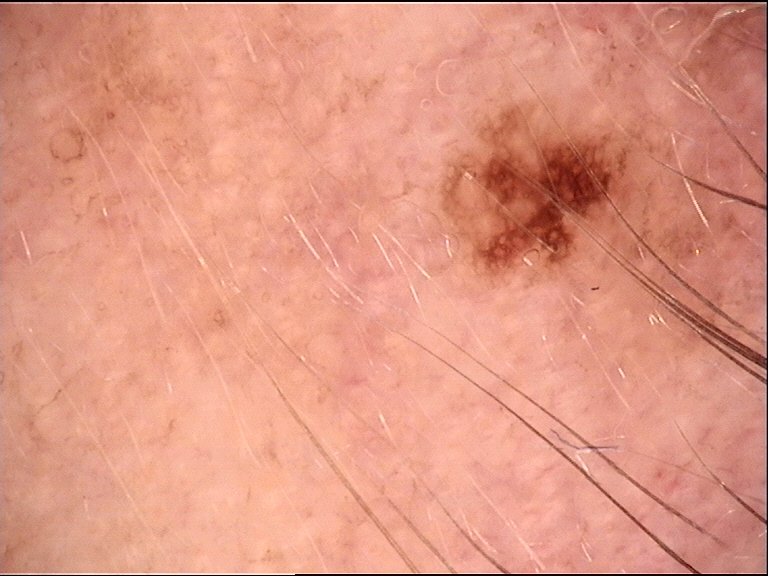{"image": "dermatoscopy", "diagnosis": {"name": "dysplastic junctional nevus", "code": "jd", "malignancy": "benign", "super_class": "melanocytic", "confirmation": "expert consensus"}}